A skin lesion imaged with a dermatoscope:
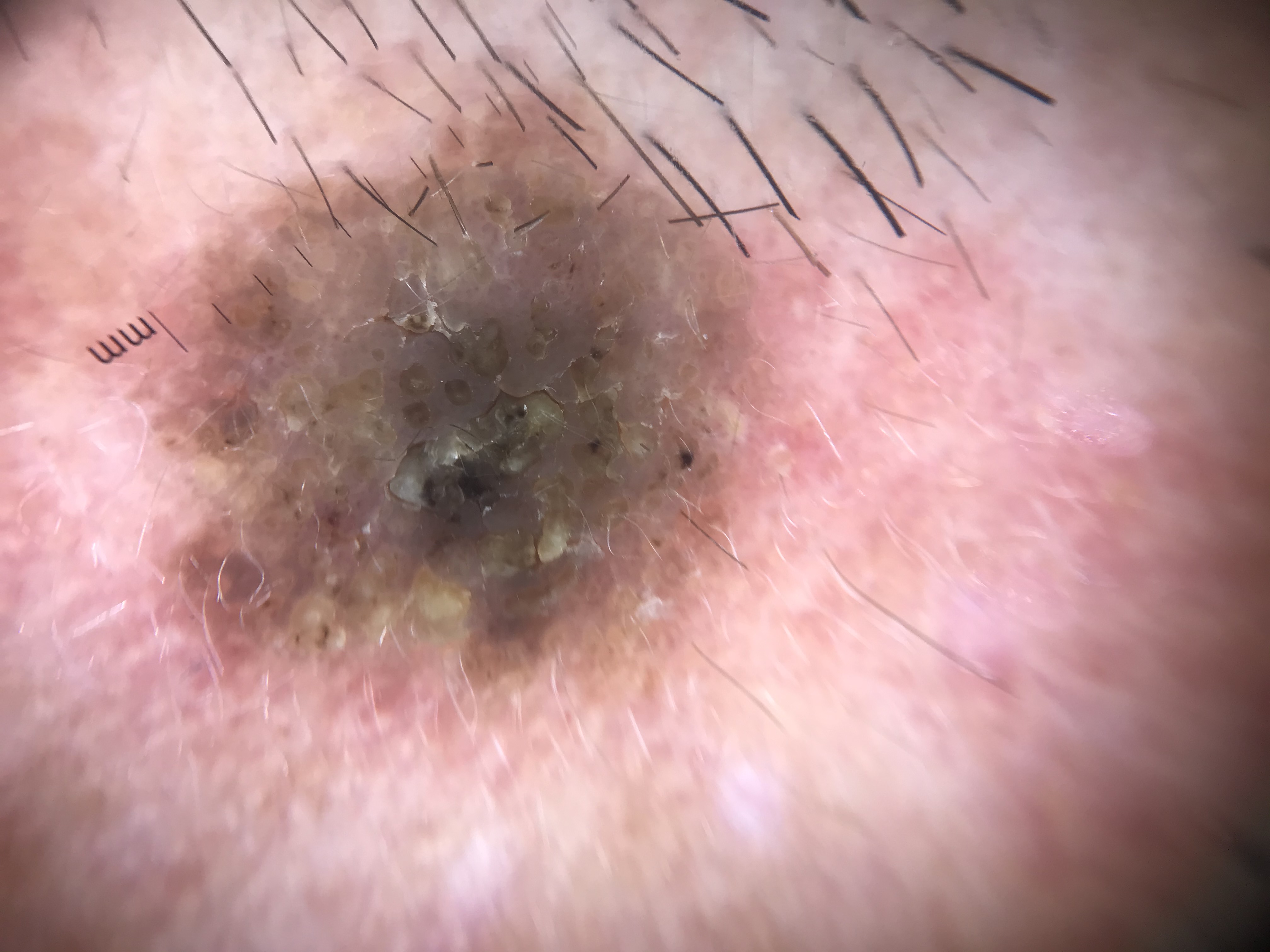Q: What is this lesion?
A: seborrheic keratosis (expert consensus)